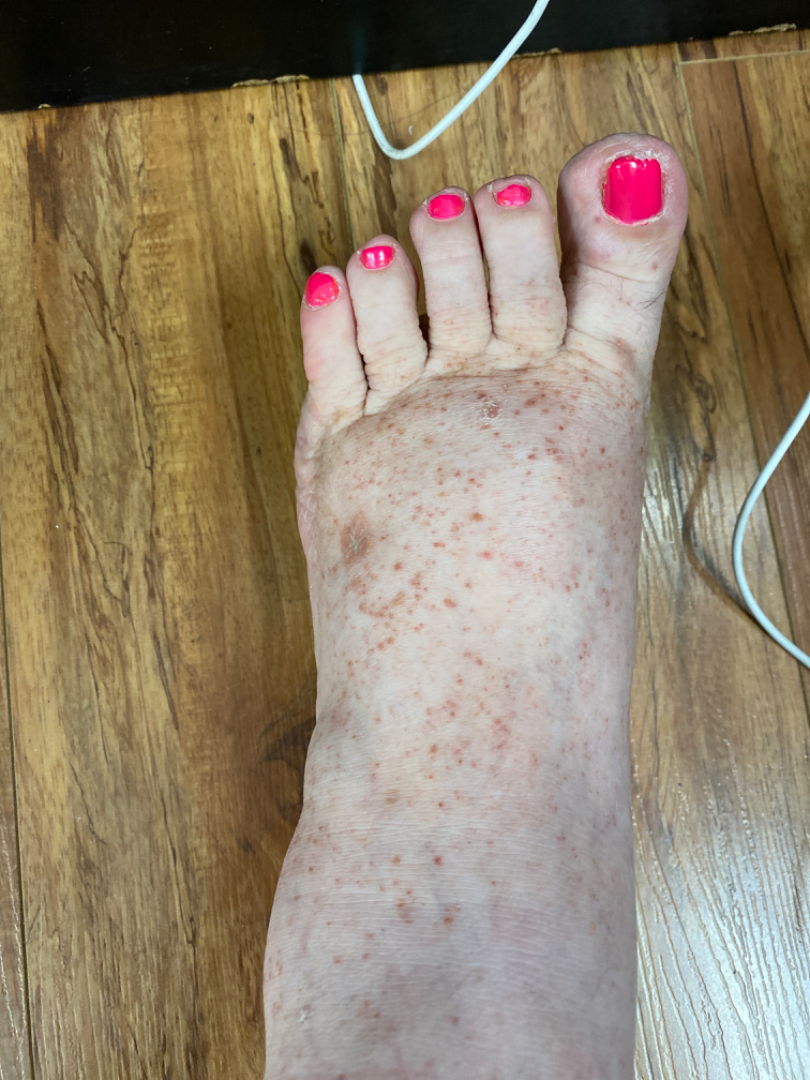skin tone=Fitzpatrick skin type III; anatomic site=leg and top or side of the foot; associated systemic symptoms=joint pain, shortness of breath and fatigue; view=close-up; symptom duration=one to three months; described texture=raised or bumpy; dermatologist impression=Pigmented purpuric eruption and Leukocytoclastic Vasculitis were each considered, in no particular order.